A dermatoscopic image of a skin lesion:
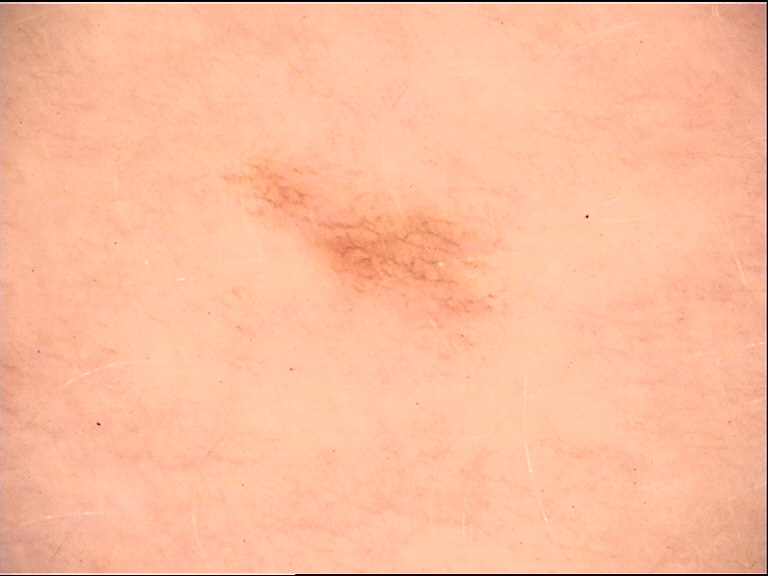diagnosis=dysplastic junctional nevus (expert consensus)